A skin lesion imaged with a dermatoscope.
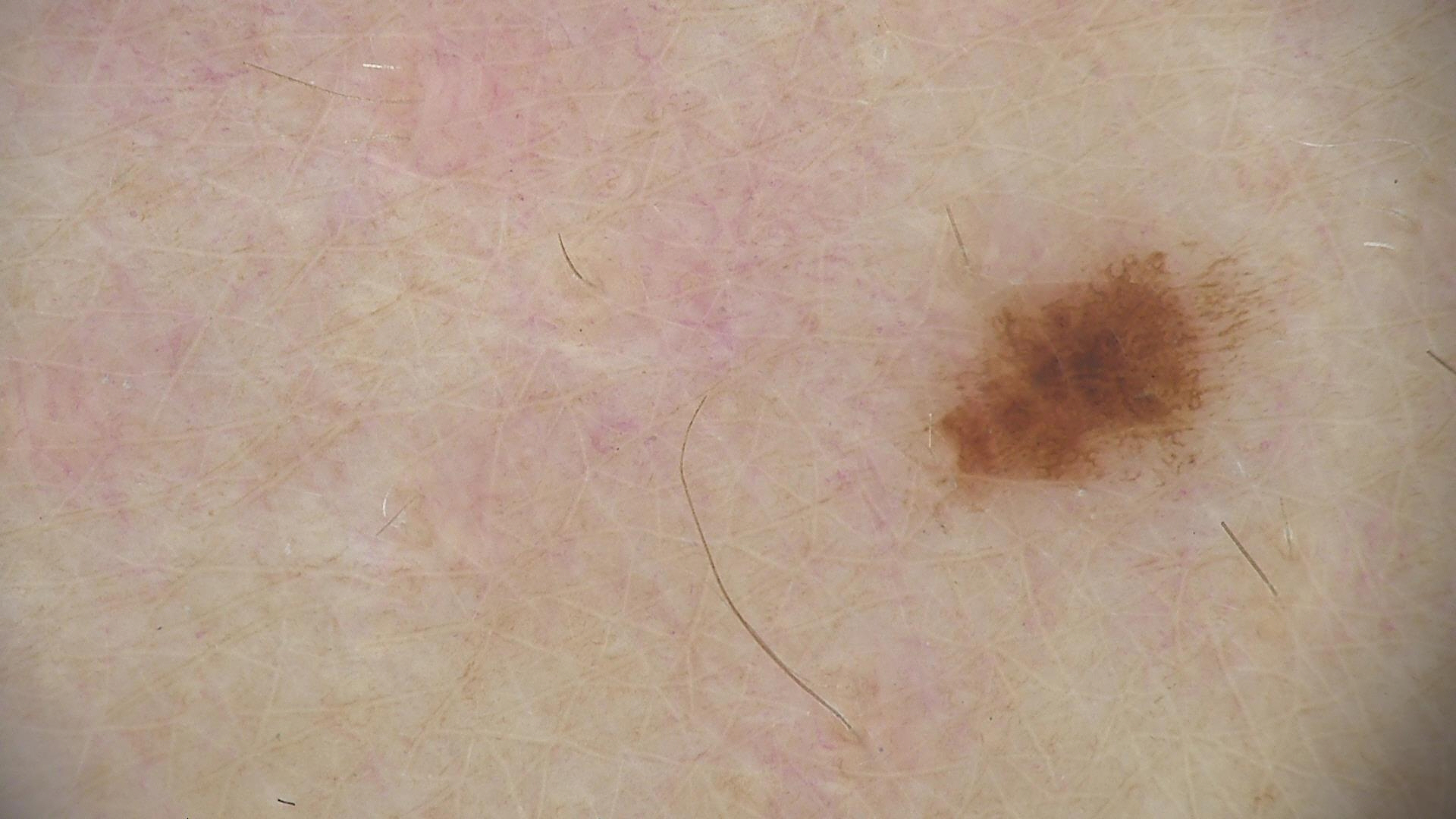Q: What is the diagnosis?
A: dysplastic junctional nevus (expert consensus)